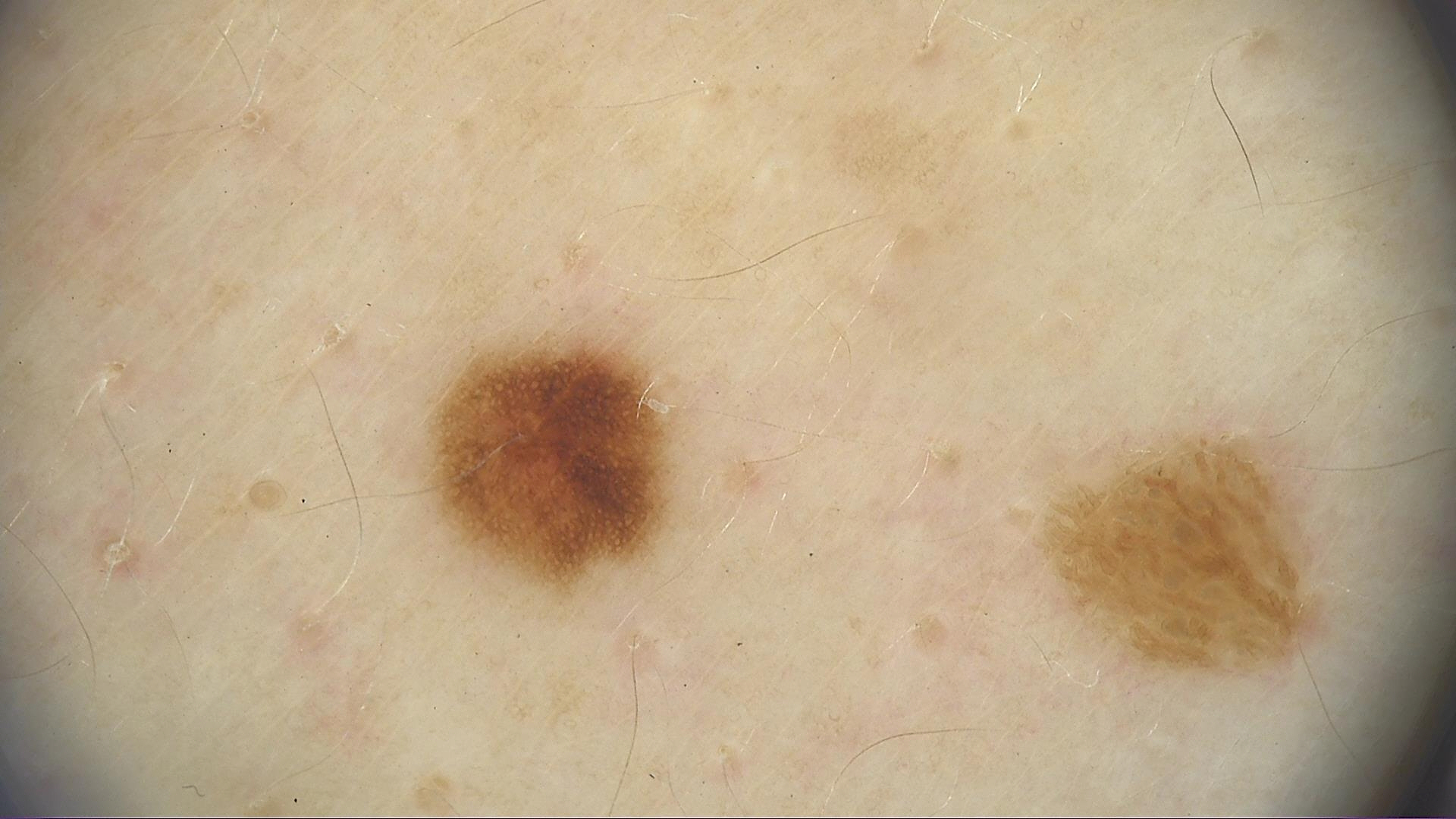label: dysplastic junctional nevus (expert consensus)